A dermoscopic photograph of a skin lesion.
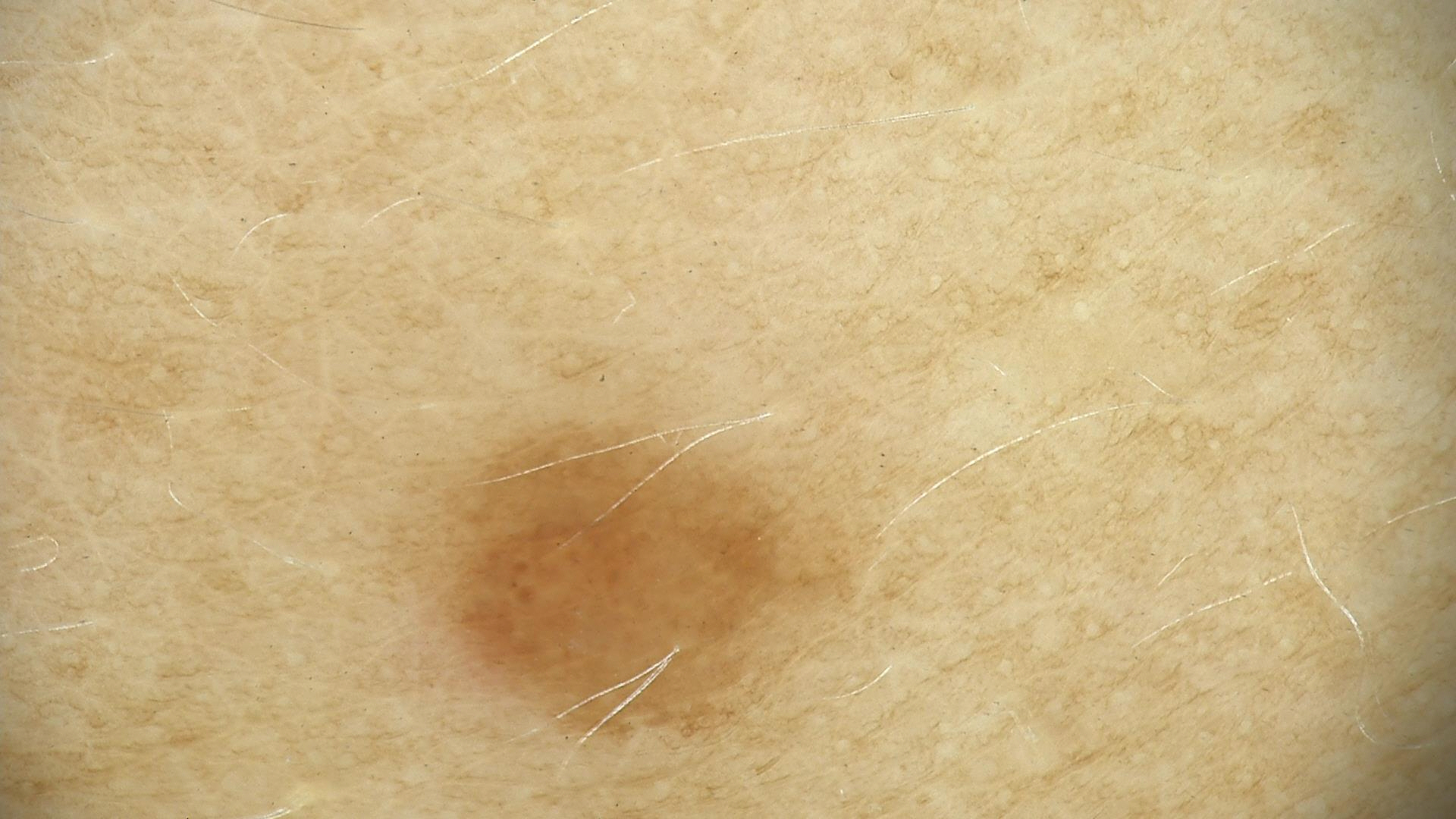Summary:
The architecture is that of a banal lesion.
Conclusion:
Consistent with a junctional nevus.